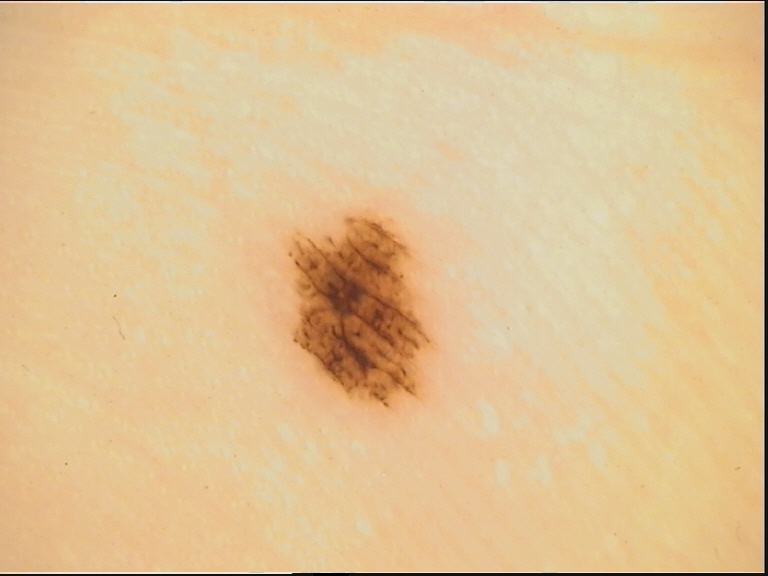A dermoscopy image of a single skin lesion. The diagnostic label was an acral dysplastic junctional nevus.